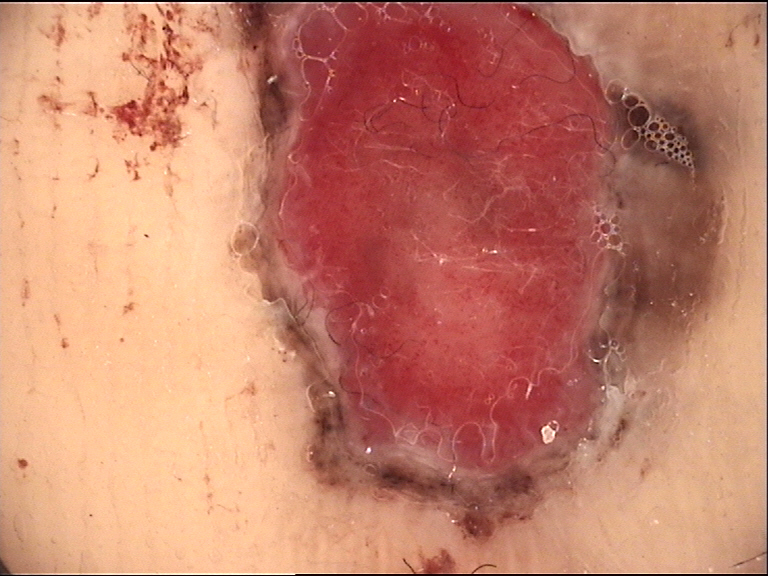Diagnosis:
Biopsy-confirmed as a skin cancer — an acral nodular melanoma.